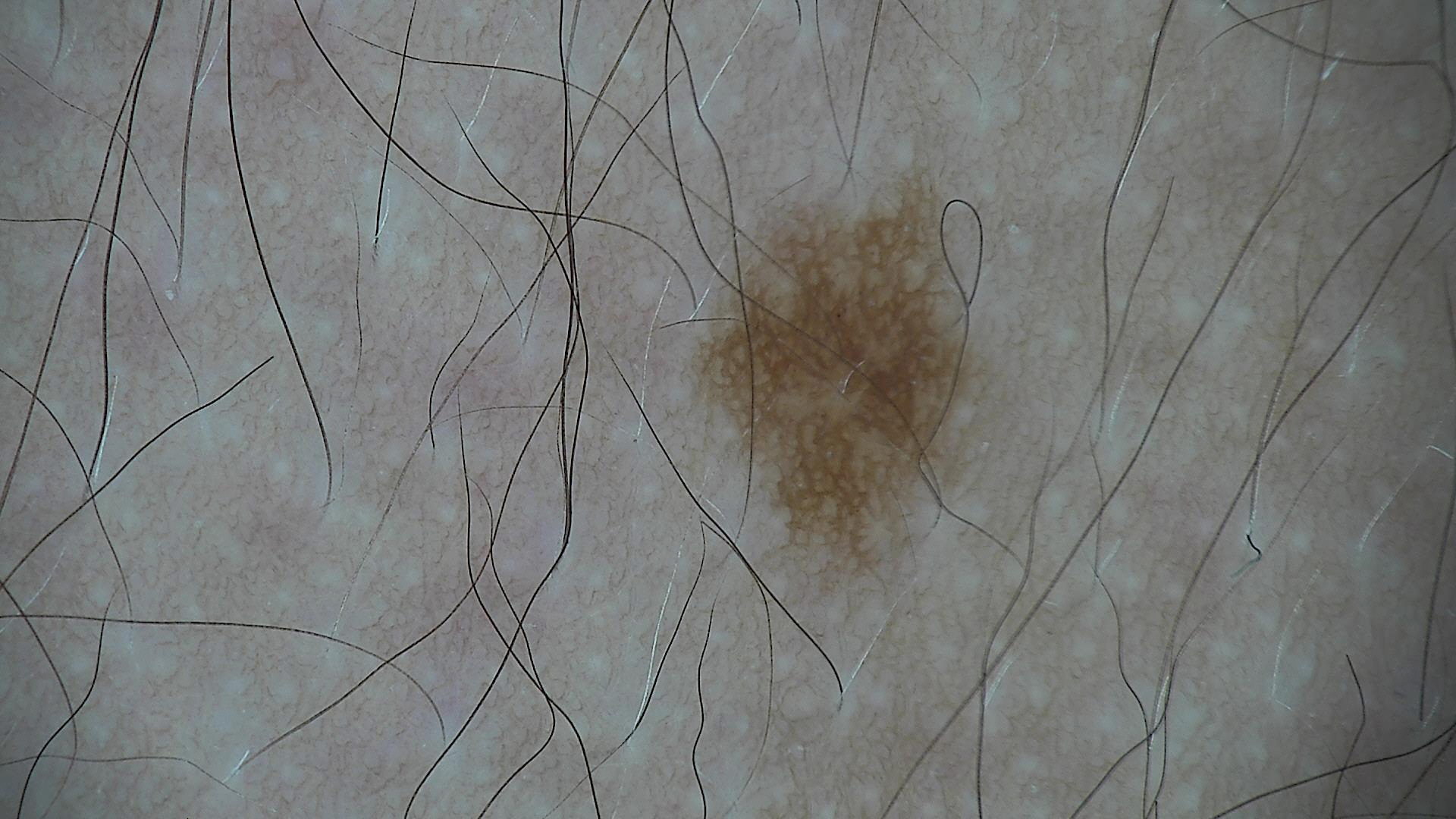assessment = dysplastic junctional nevus (expert consensus).